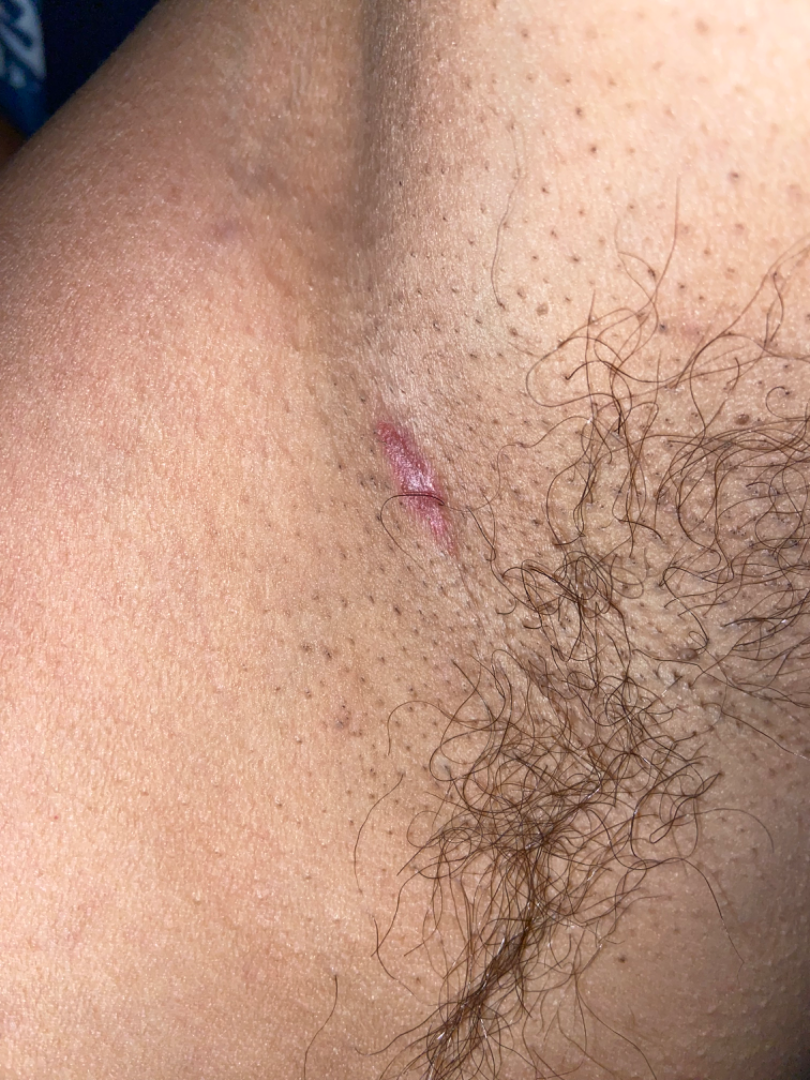The reviewer was unable to grade this case for skin condition.
The lesion is associated with bothersome appearance, pain and burning.
The patient described the issue as a rash.
The photo was captured at a distance.
Fitzpatrick phototype IV; non-clinician graders estimated Monk skin tone scale 5 (US pool) or 2 (India pool).
The condition has been present for one to four weeks.
The arm is involved.
The lesion is described as flat and rough or flaky.